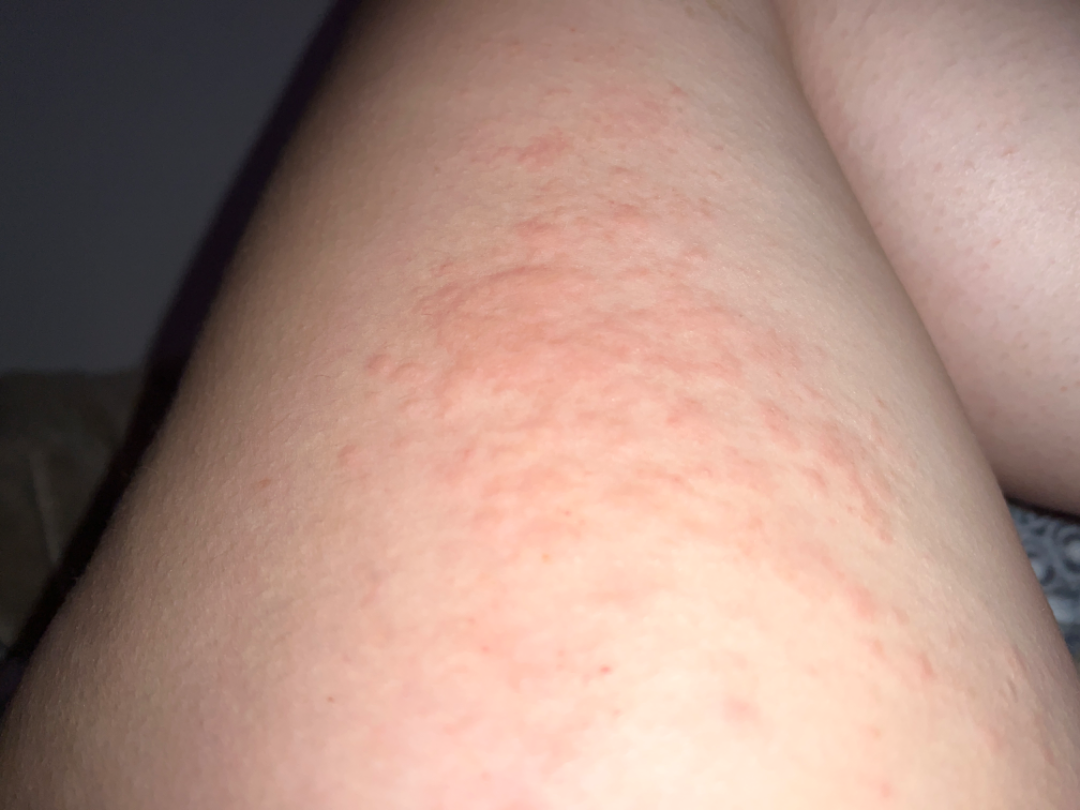  shot_type: at a distance
  symptoms:
    - bothersome appearance
    - enlargement
    - itching
  duration: less than one week
  patient: female, age 18–29
  texture: raised or bumpy
  systemic_symptoms: none reported
  patient_category: a rash
  body_site: leg
  differential:
    leading:
      - Acute dermatitis, NOS